Dermoscopy of a skin lesion; a male patient roughly 75 years of age.
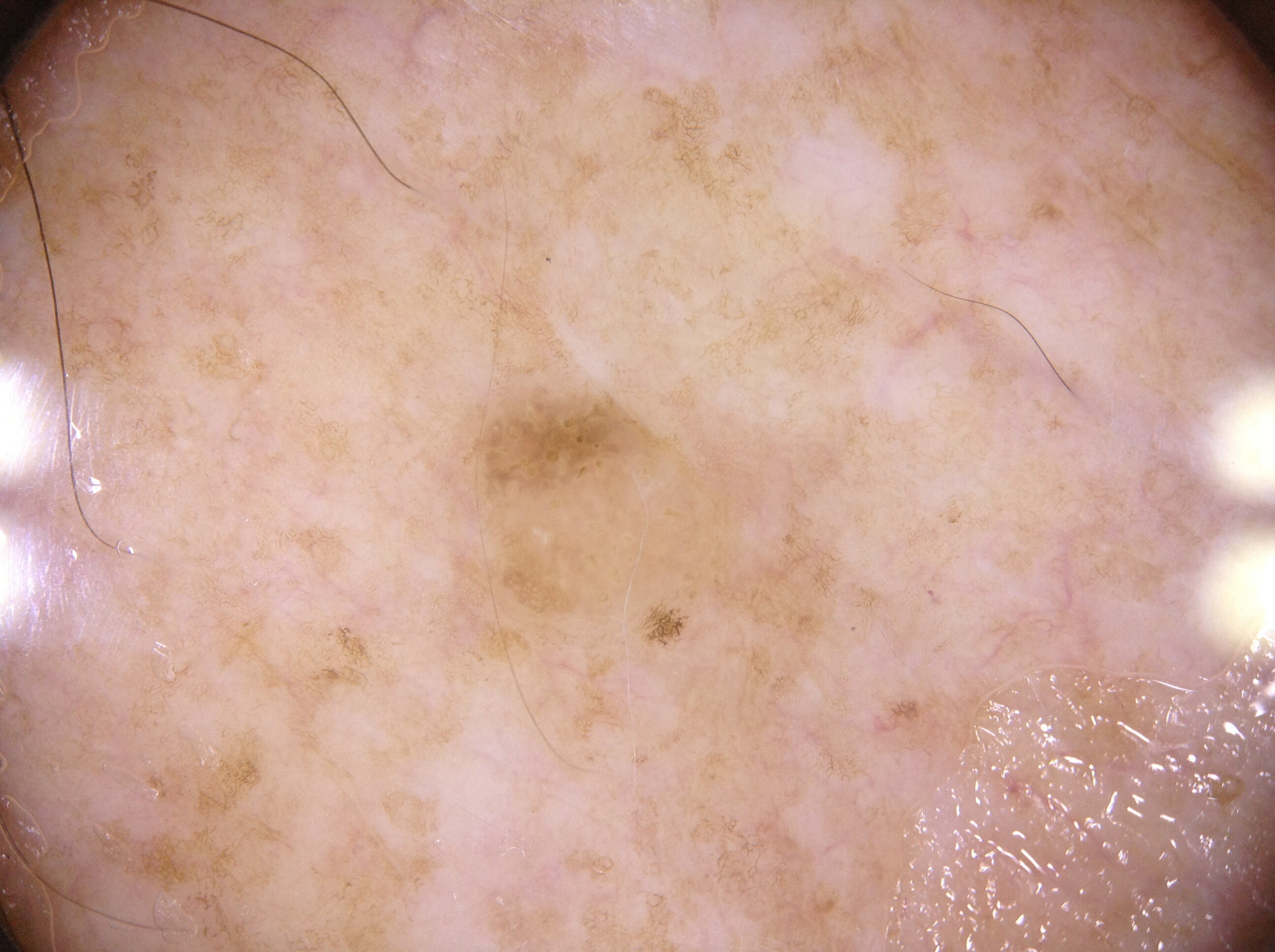{"dermoscopic_features": {"present": ["pigment network", "milia-like cysts"], "absent": ["negative network", "streaks"]}, "lesion_location": {"bbox_xyxy": [418, 354, 748, 701]}, "diagnosis": {"name": "seborrheic keratosis", "malignancy": "benign", "lineage": "keratinocytic", "provenance": "clinical"}}